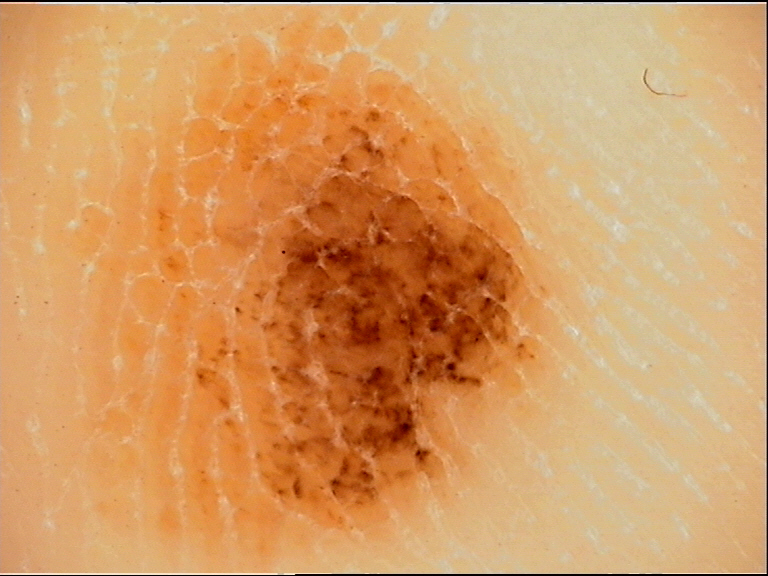A dermoscopic image of a skin lesion.
Consistent with an acral dysplastic compound nevus.